A patient aged 35 · a clinical photograph showing a skin lesion:
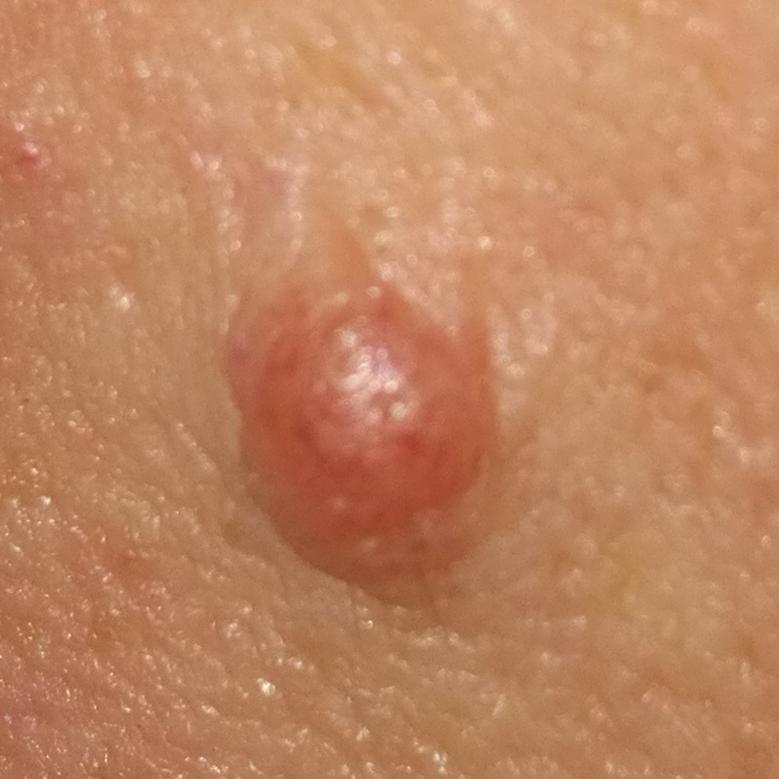region = the face | symptoms = elevation, growth, itching | assessment = nevus (clinical consensus).